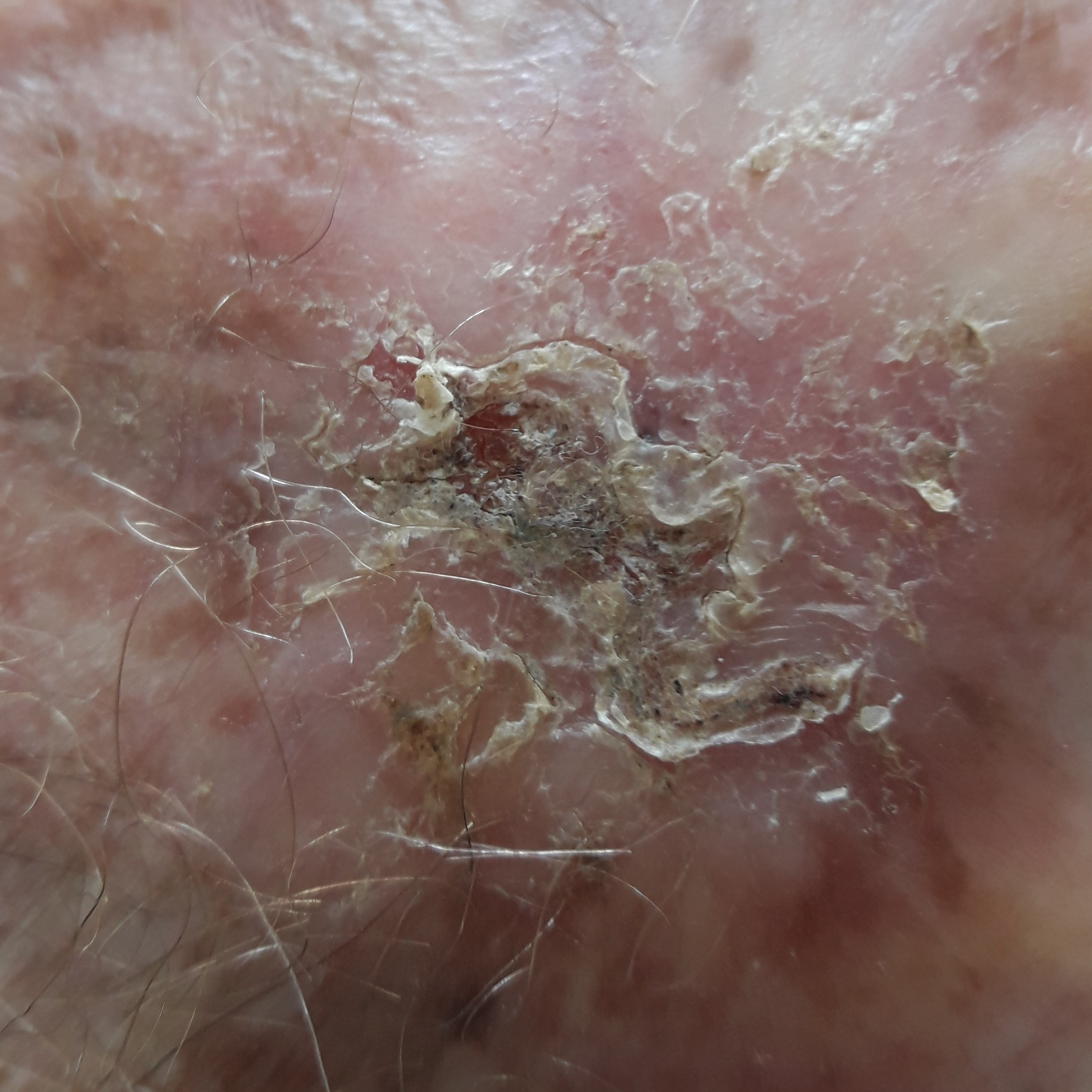{"diagnosis": {"name": "basal cell carcinoma", "code": "BCC", "malignancy": "malignant", "confirmation": "histopathology"}}